FST V, the contributor notes itching and enlargement, close-up view, present for about one day, no constitutional symptoms were reported, self-categorized by the patient as a rash, located on the arm:
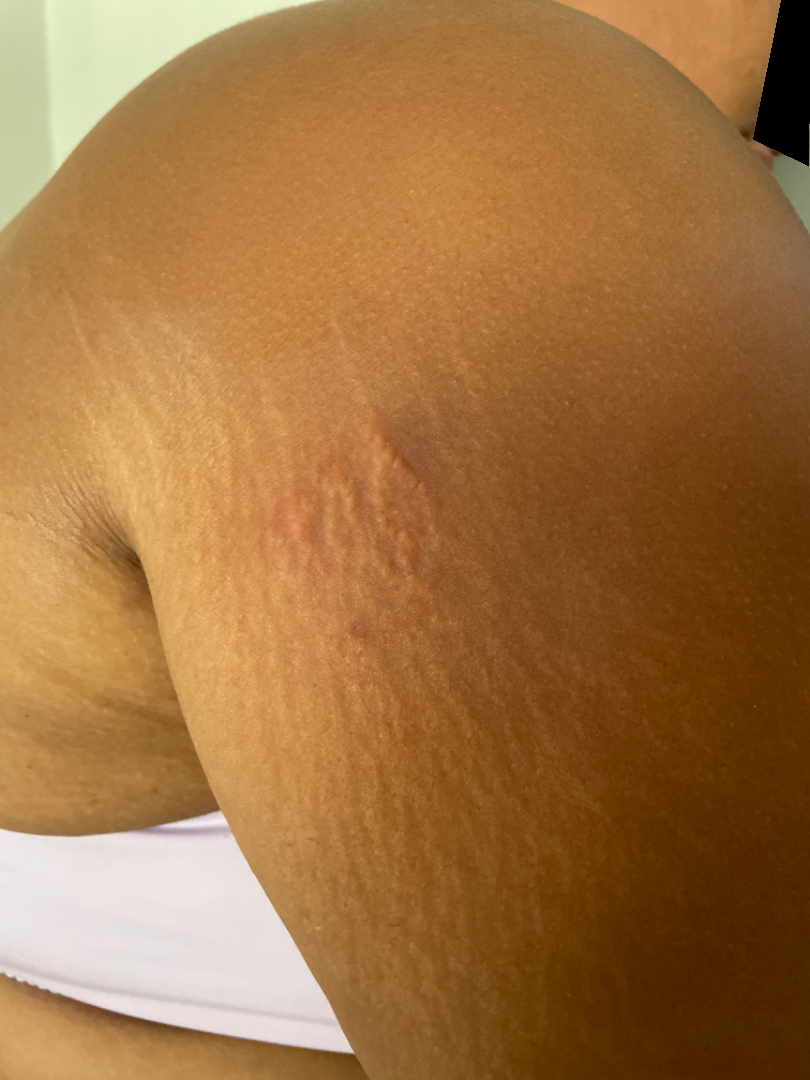The skin findings could not be characterized from the image.